A dermoscopic photograph of a skin lesion: 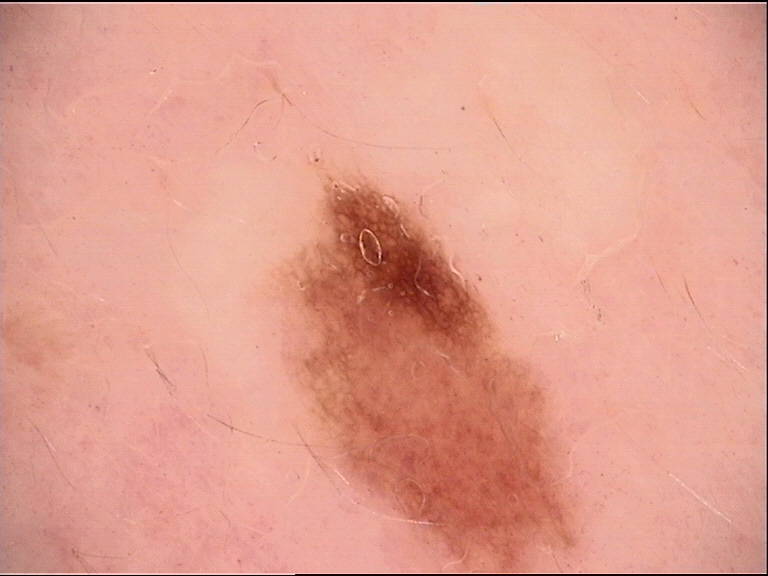Case:
• label: dysplastic junctional nevus (expert consensus)